A male subject in their early 70s.
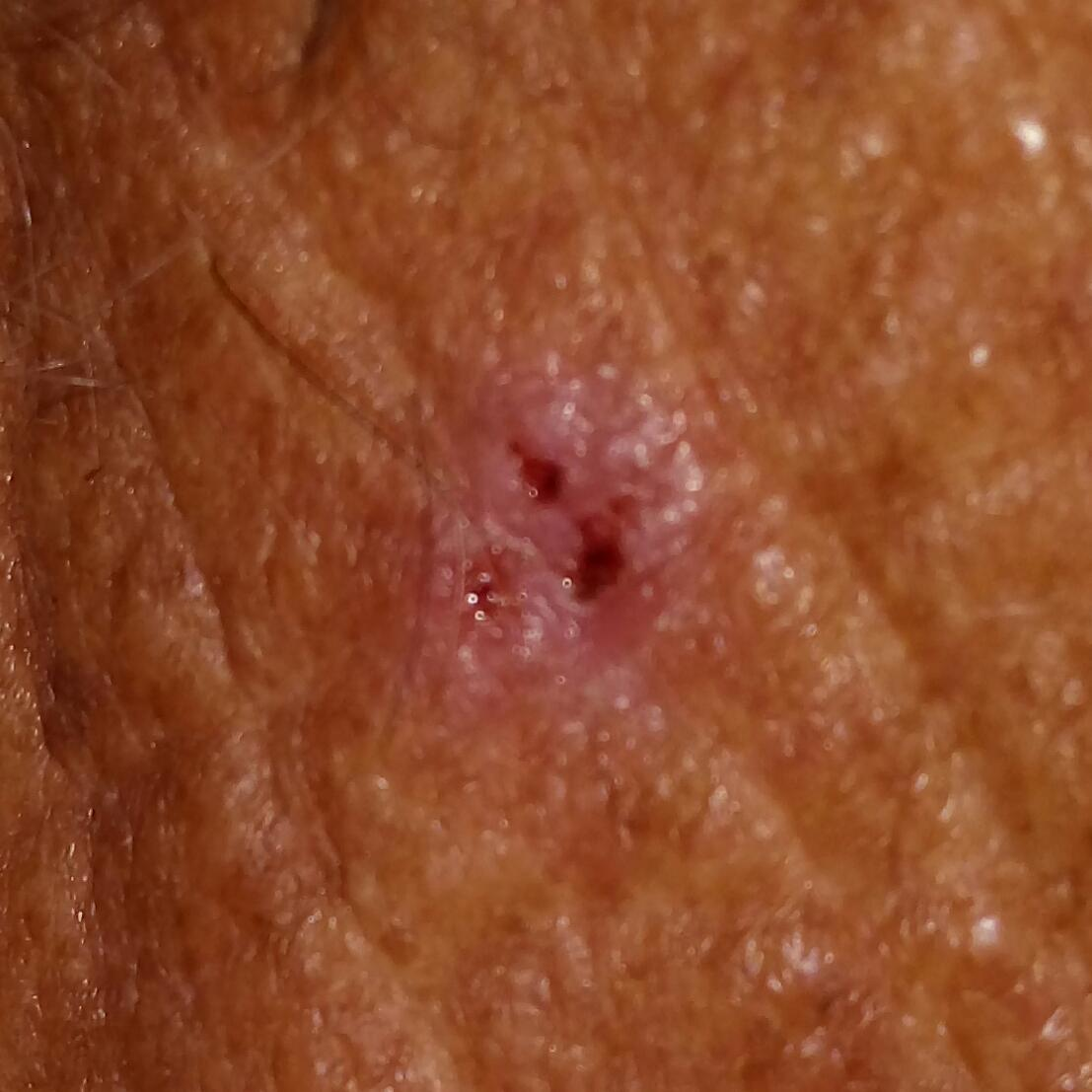Q: Where on the body is the lesion?
A: the neck
Q: What does the patient describe?
A: elevation, itching, bleeding / no growth
Q: What is the diagnosis?
A: basal cell carcinoma (biopsy-proven)